A dermoscopic image of a skin lesion.
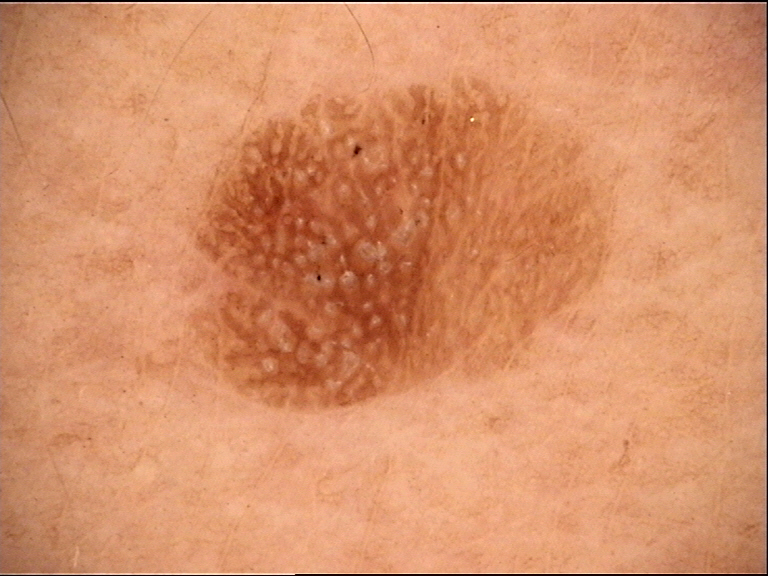category — keratinocytic | diagnosis — seborrheic keratosis (expert consensus).